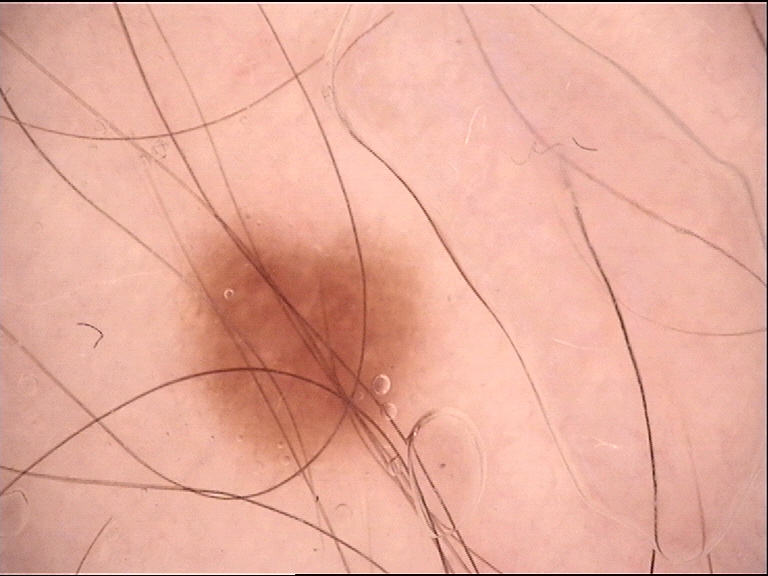A skin lesion imaged with a dermatoscope. Diagnosed as a benign lesion — a dysplastic junctional nevus.